Recorded as Fitzpatrick skin type II. A dermoscopic photograph of a skin lesion.
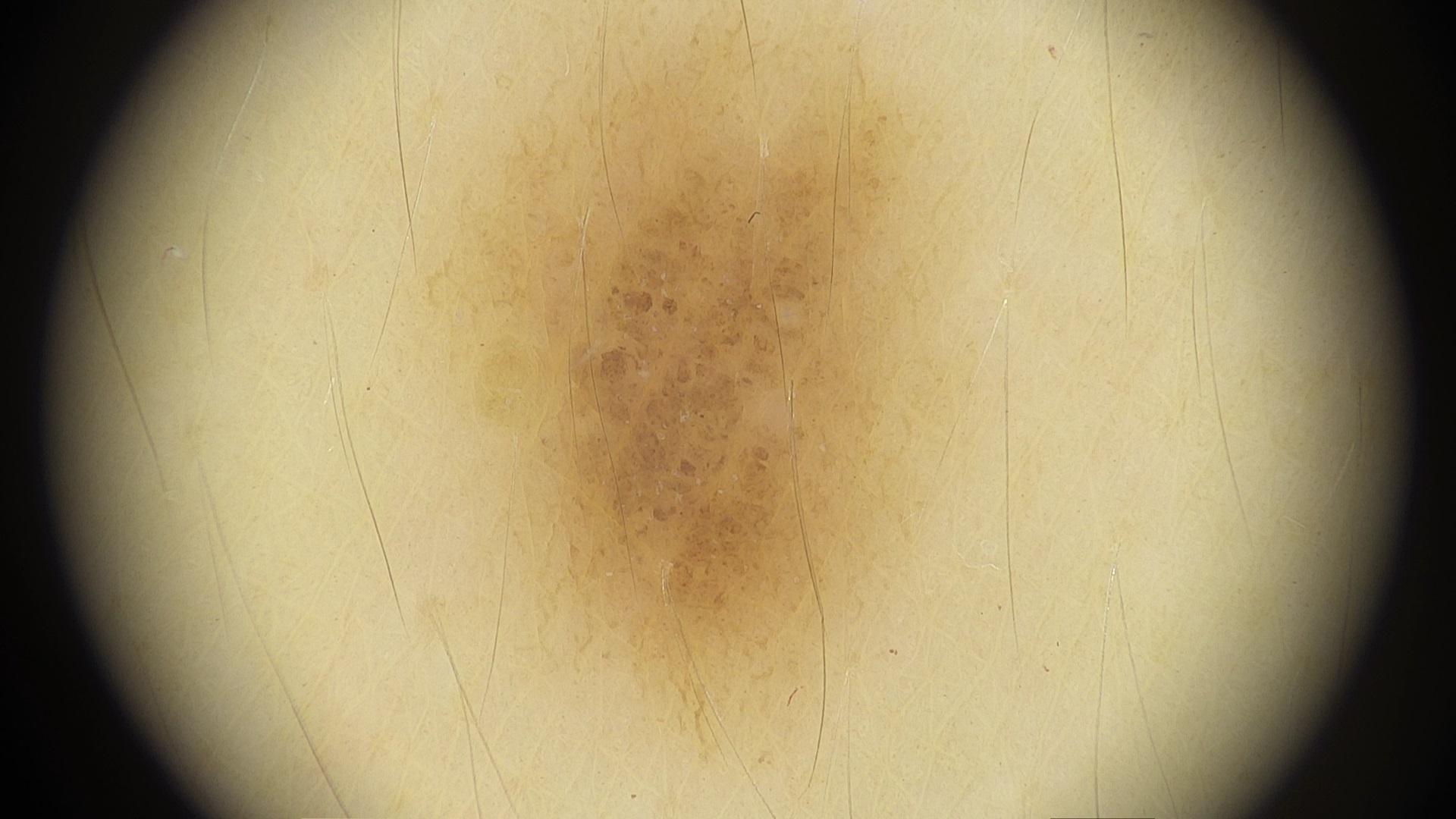The diagnostic impression was a melanocytic lesion — a nevus.